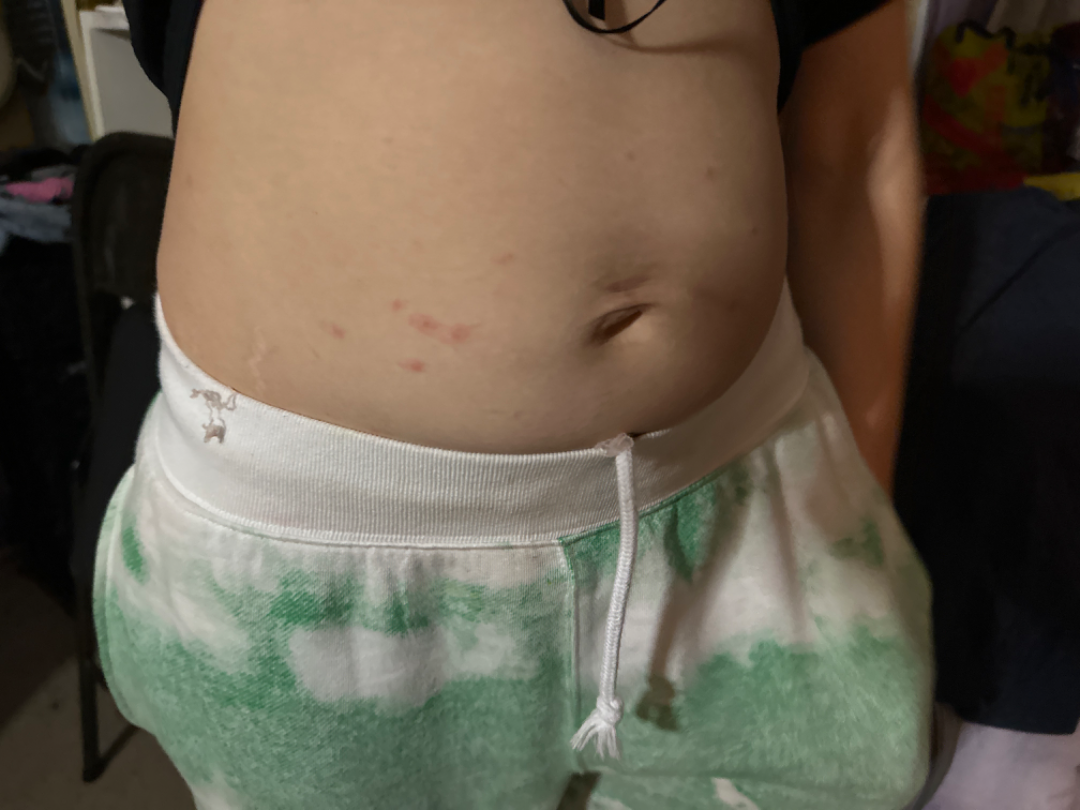Q: Image view?
A: at a distance
Q: Patient demographics?
A: female, age 18–29
Q: What is the dermatologist's impression?
A: Scabies (considered); Insect Bite (considered)